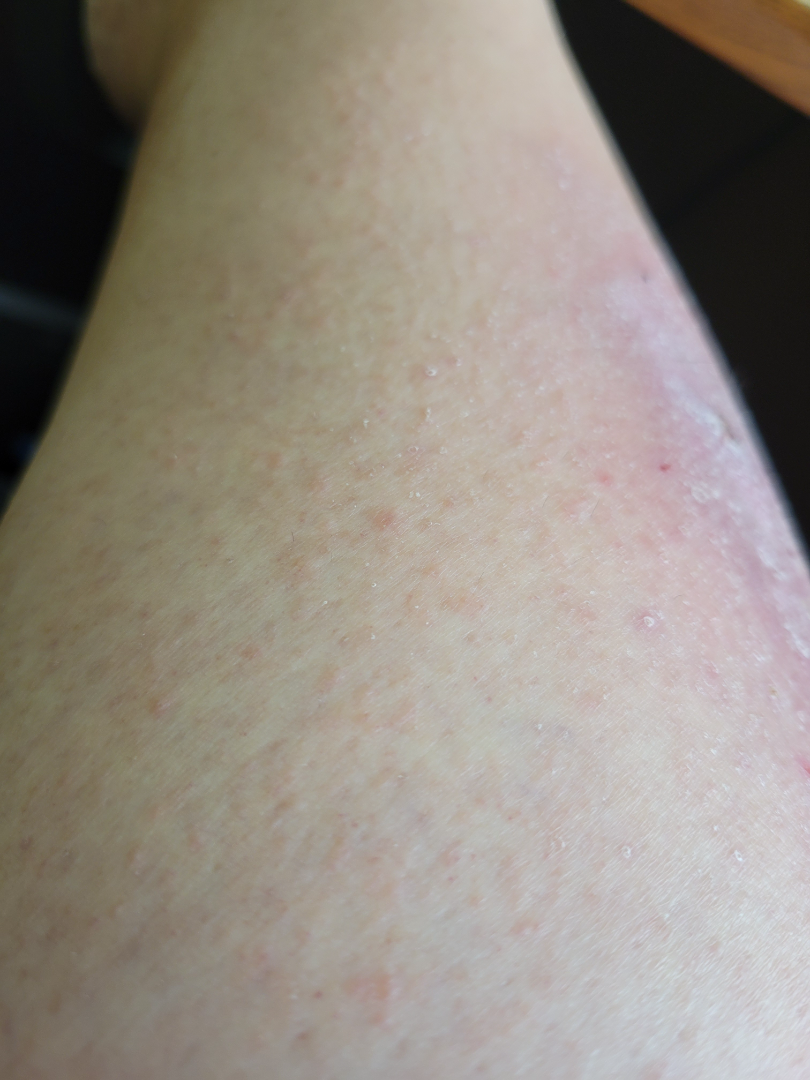duration = one to four weeks | photo taken = close-up | associated systemic symptoms = none reported | patient-reported symptoms = bothersome appearance, pain, burning and enlargement | affected area = leg | described texture = raised or bumpy | differential diagnosis = favoring Eczema; an alternative is Psoriasis; with consideration of Allergic Contact Dermatitis.